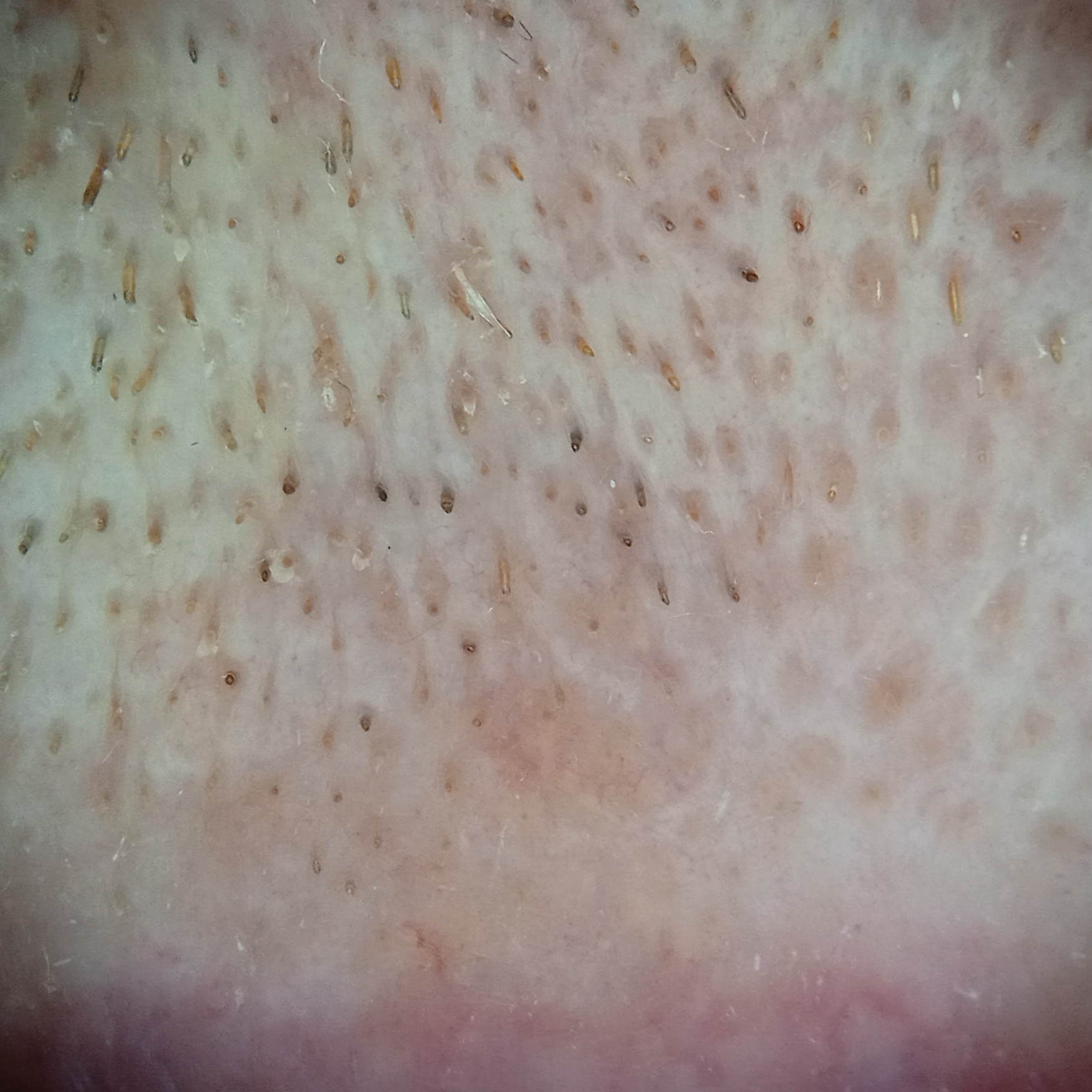image — dermatoscopic image; sun reaction — skin reddens with sun exposure; nevus count — a moderate number of melanocytic nevi; relevant history — a personal history of cancer, a personal history of skin cancer; subject — male, aged 77; size — 6.4 mm; diagnosis — actinic keratosis (dermatologist consensus).